A dermoscopic close-up of a skin lesion; the patient is a male aged around 80: 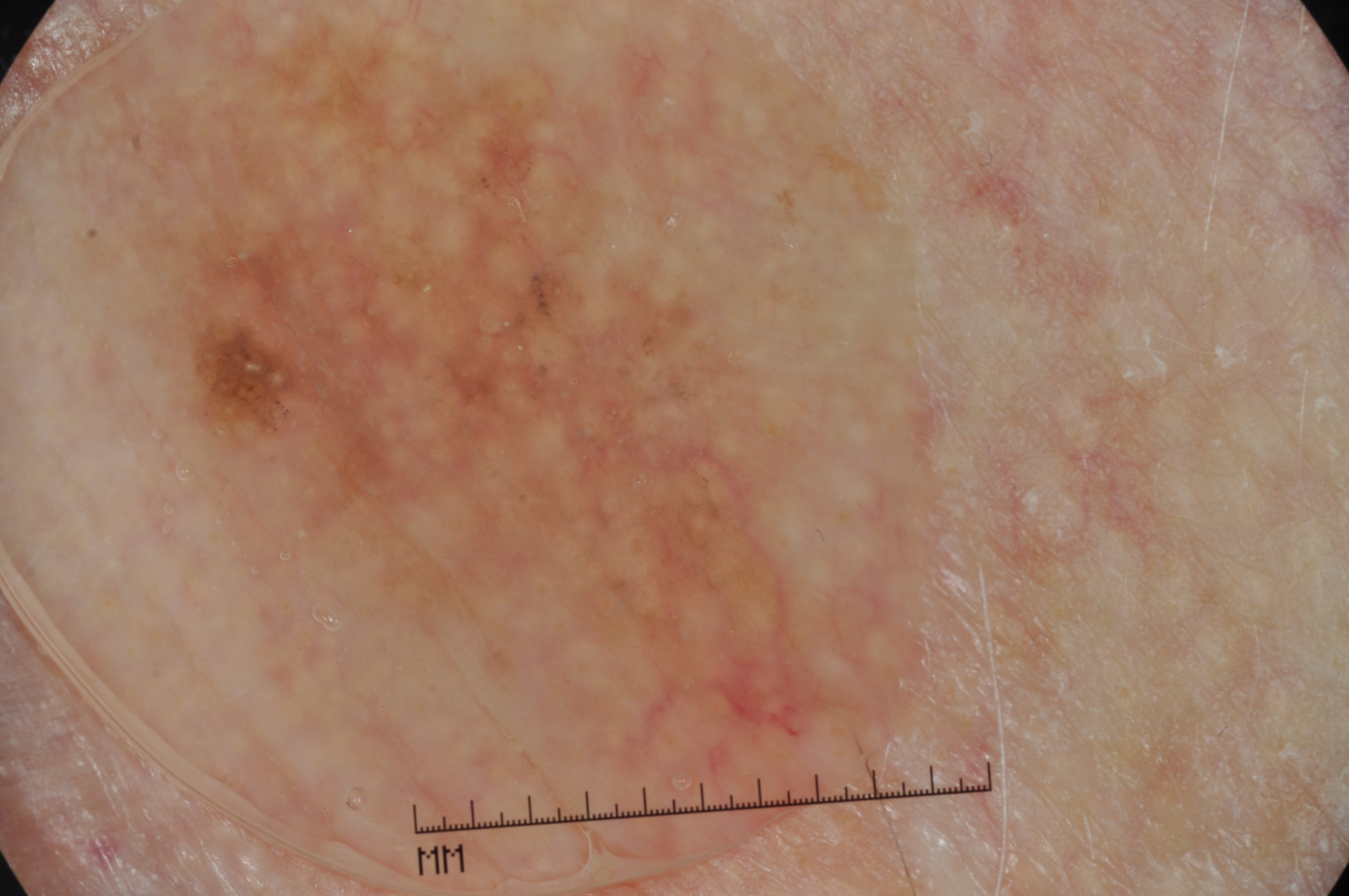{
  "lesion_location": {
    "bbox_xyxy": [
      75,
      5,
      845,
      859
    ]
  },
  "lesion_extent": {
    "approx_field_fraction_pct": 39
  },
  "dermoscopic_features": {
    "present": [
      "milia-like cysts",
      "pigment network"
    ],
    "absent": [
      "negative network",
      "streaks"
    ]
  },
  "diagnosis": {
    "name": "melanoma",
    "malignancy": "malignant",
    "lineage": "melanocytic",
    "provenance": "histopathology"
  }
}